The patient described the issue as a rash. The photograph was taken at a distance. The subject is 40–49, female. The lesion is associated with enlargement, itching and bothersome appearance. Present for less than one week. The lesion is described as fluid-filled. The back of the hand is involved. No constitutional symptoms were reported:
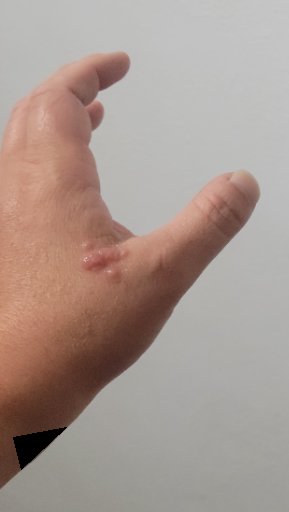Findings:
The case was indeterminate on photographic review.